The patient was assessed as Fitzpatrick III. A skin lesion imaged with a dermatoscope. A male subject in their 40s. Per the chart, melanoma in a first-degree relative — 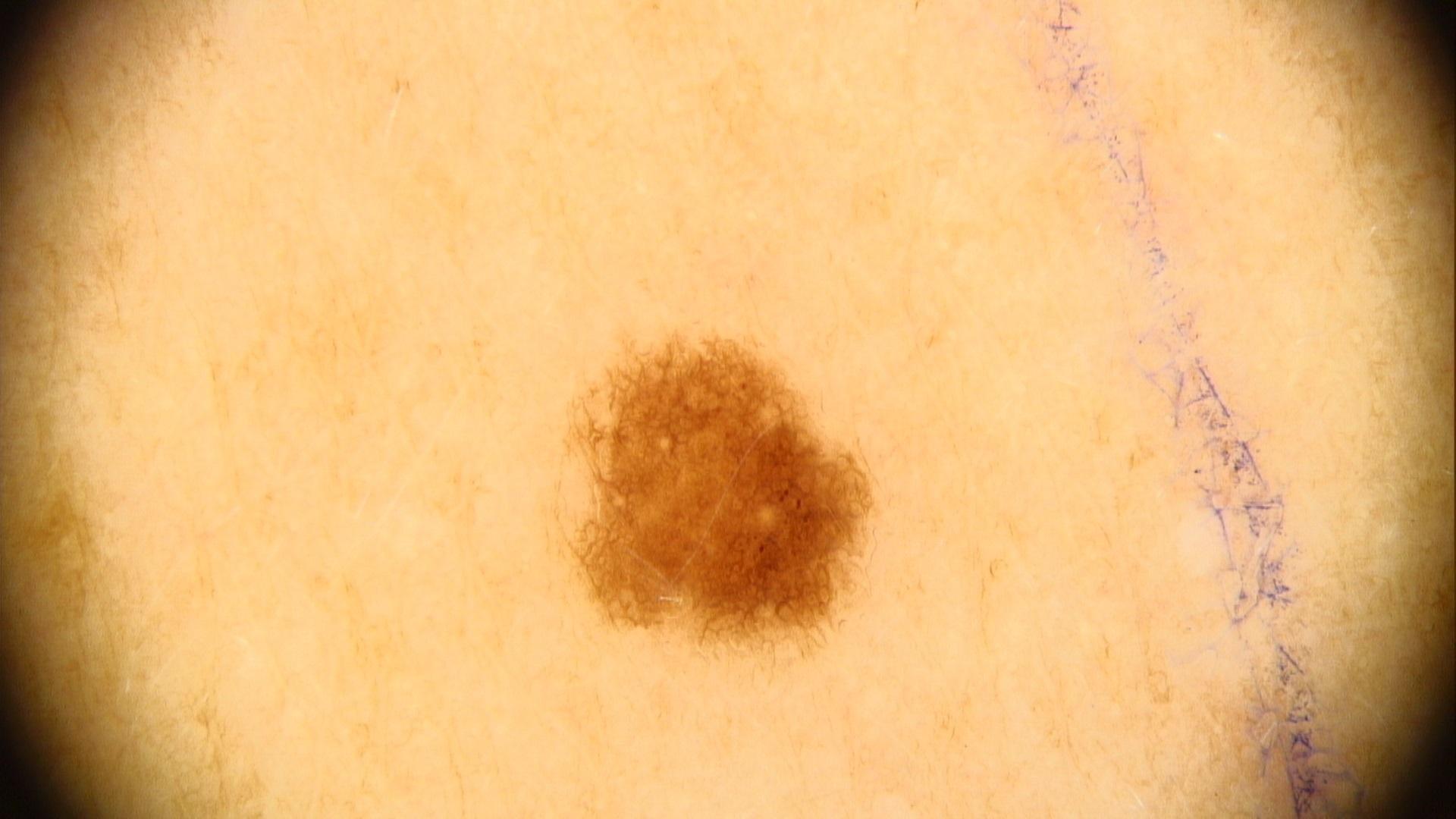The clinical impression was a benign lesion — a nevus.